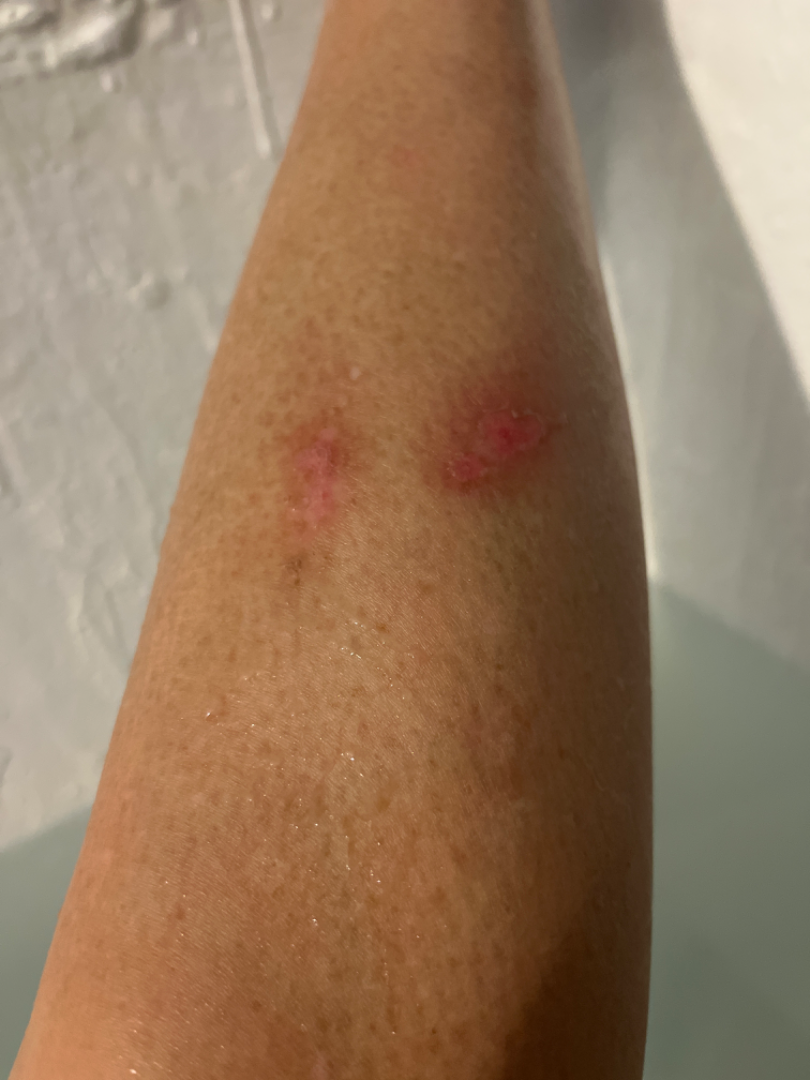Abrasion, scrape, or scab (most likely); Burn erythema of lower leg (considered).